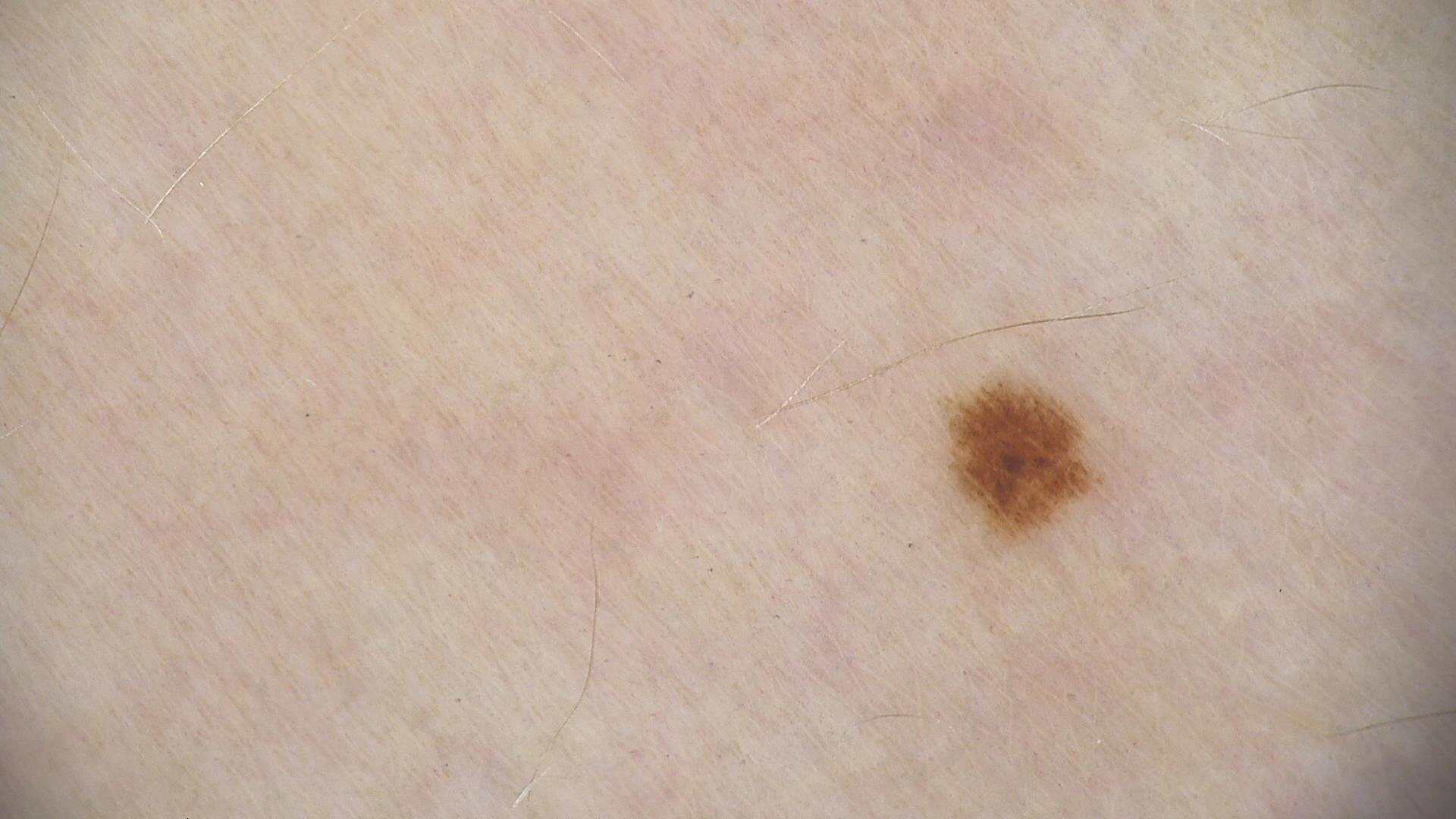A dermoscopic close-up of a skin lesion. Diagnosed as a benign lesion — a dysplastic junctional nevus.